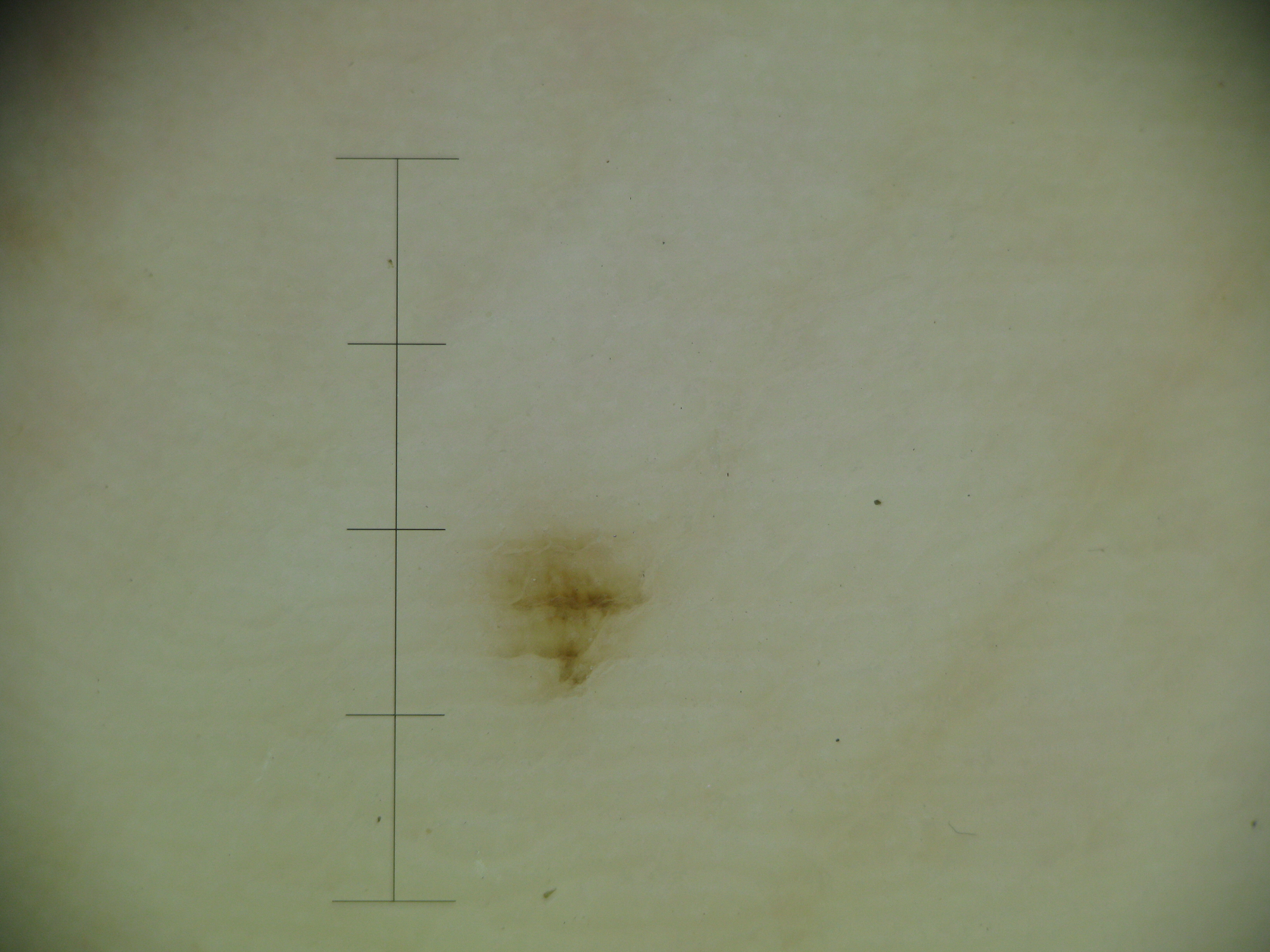Case: The morphology is that of a banal lesion. Impression: Consistent with an acral junctional nevus.